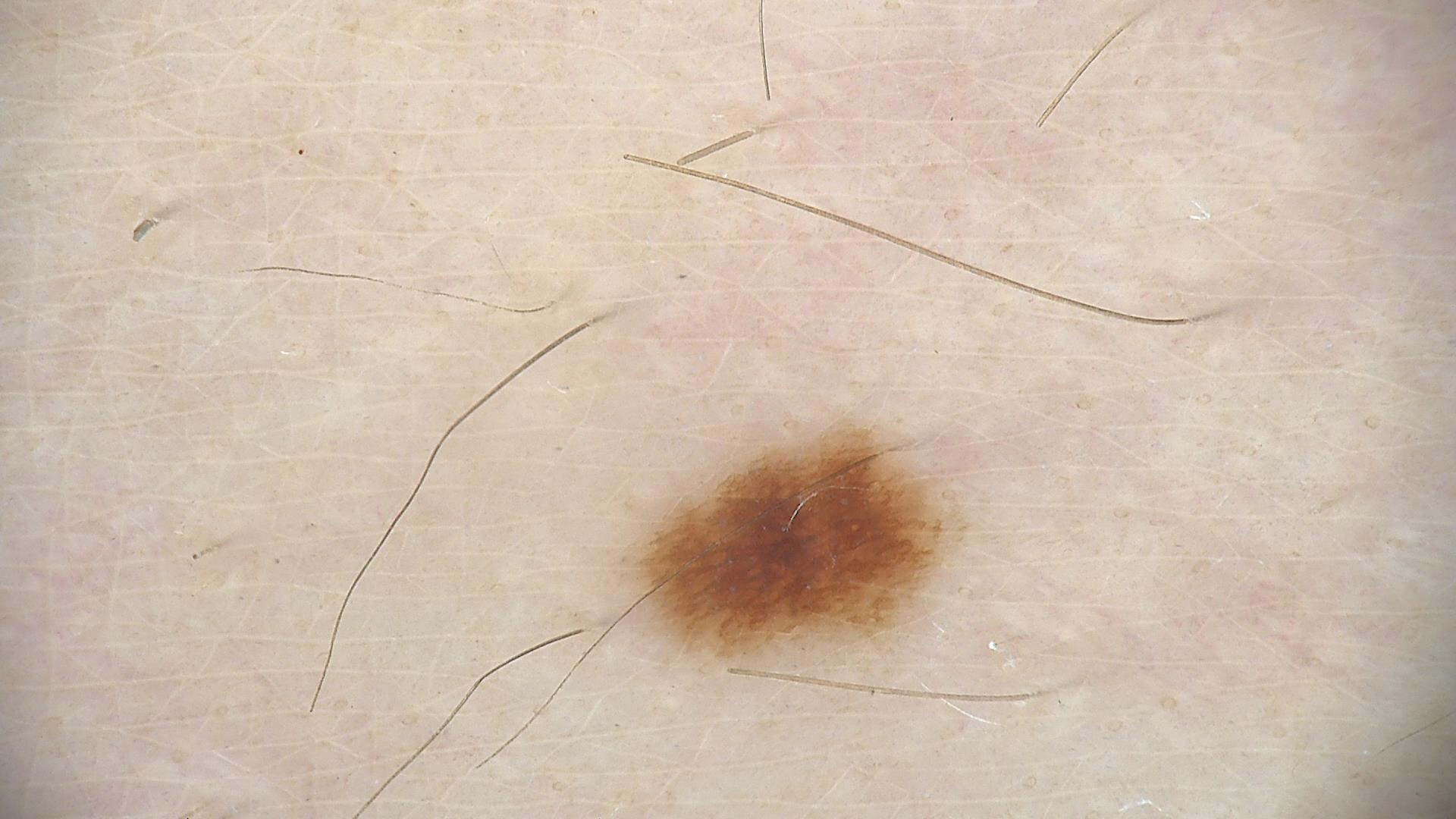A dermatoscopic image of a skin lesion.
The diagnosis was a benign lesion — a dysplastic junctional nevus.